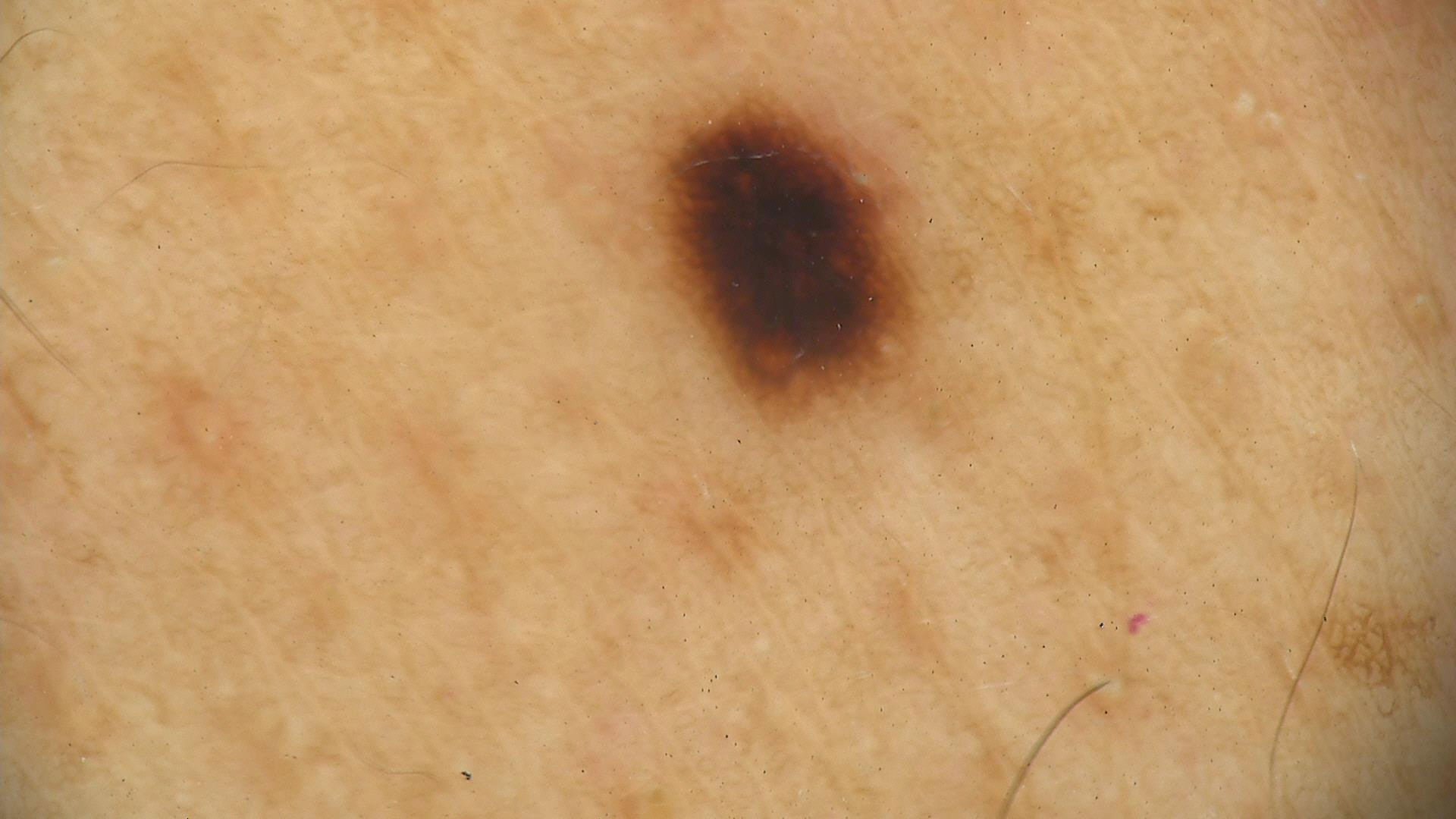Summary:
A dermoscopic close-up of a skin lesion.
Conclusion:
The diagnostic label was a benign lesion — a dysplastic junctional nevus.